Per the chart, a prior melanoma · a male patient aged around 70 · FST I · a dermatoscopic image of a skin lesion: 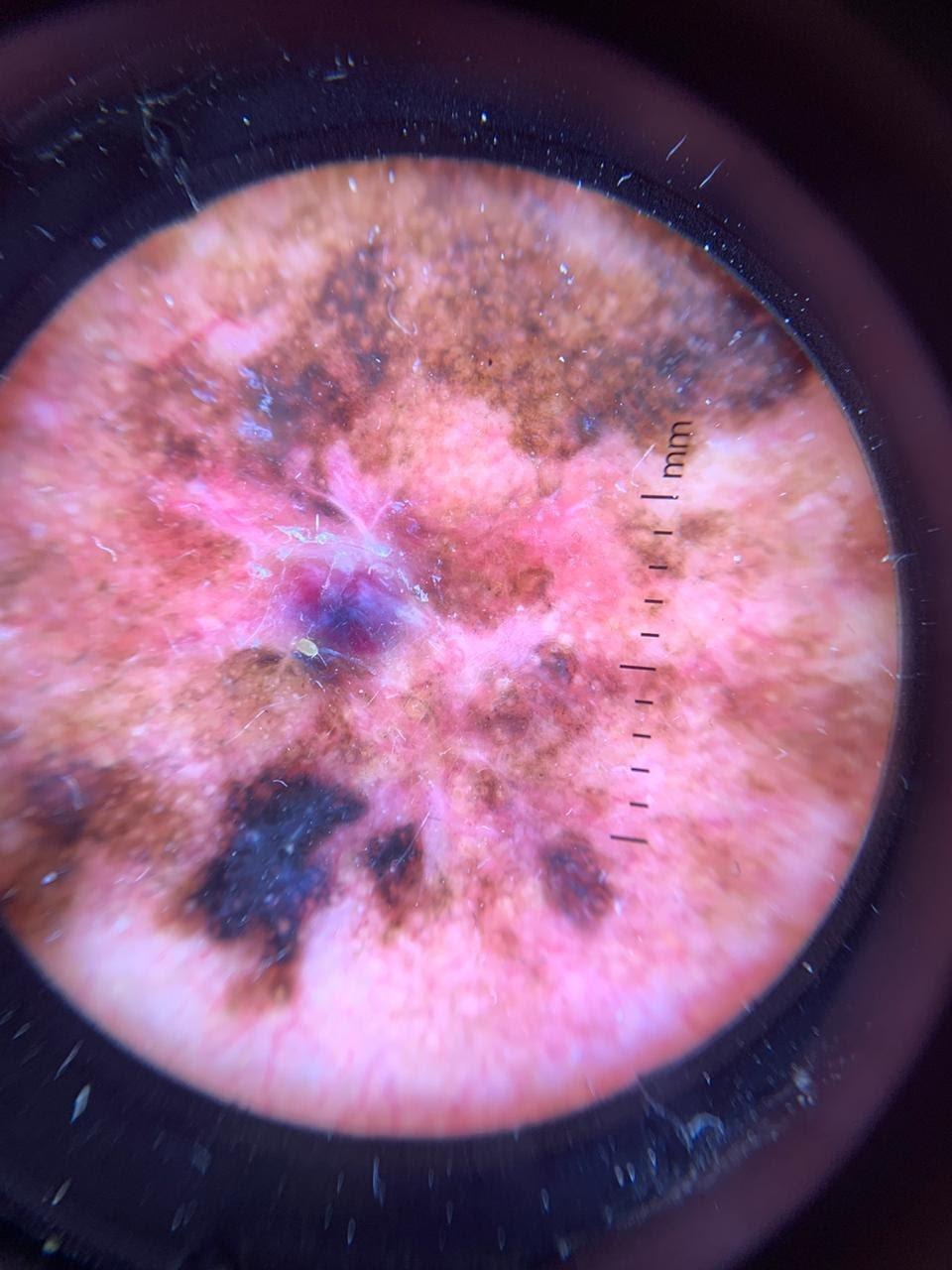{"lesion_location": {"region": "the head or neck"}, "diagnosis": {"name": "Melanoma", "malignancy": "malignant", "confirmation": "histopathology"}}